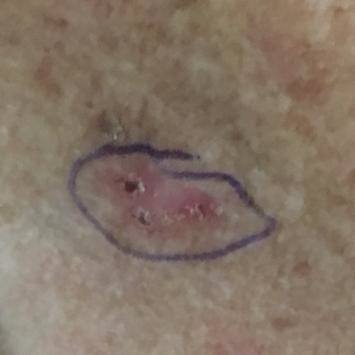| key | value |
|---|---|
| imaging | clinical photograph |
| subject | aged 70 |
| anatomic site | the chest |
| reported symptoms | itching / no elevation, no pain |
| diagnostic label | actinic keratosis (clinical consensus) |